A male subject roughly 80 years of age — 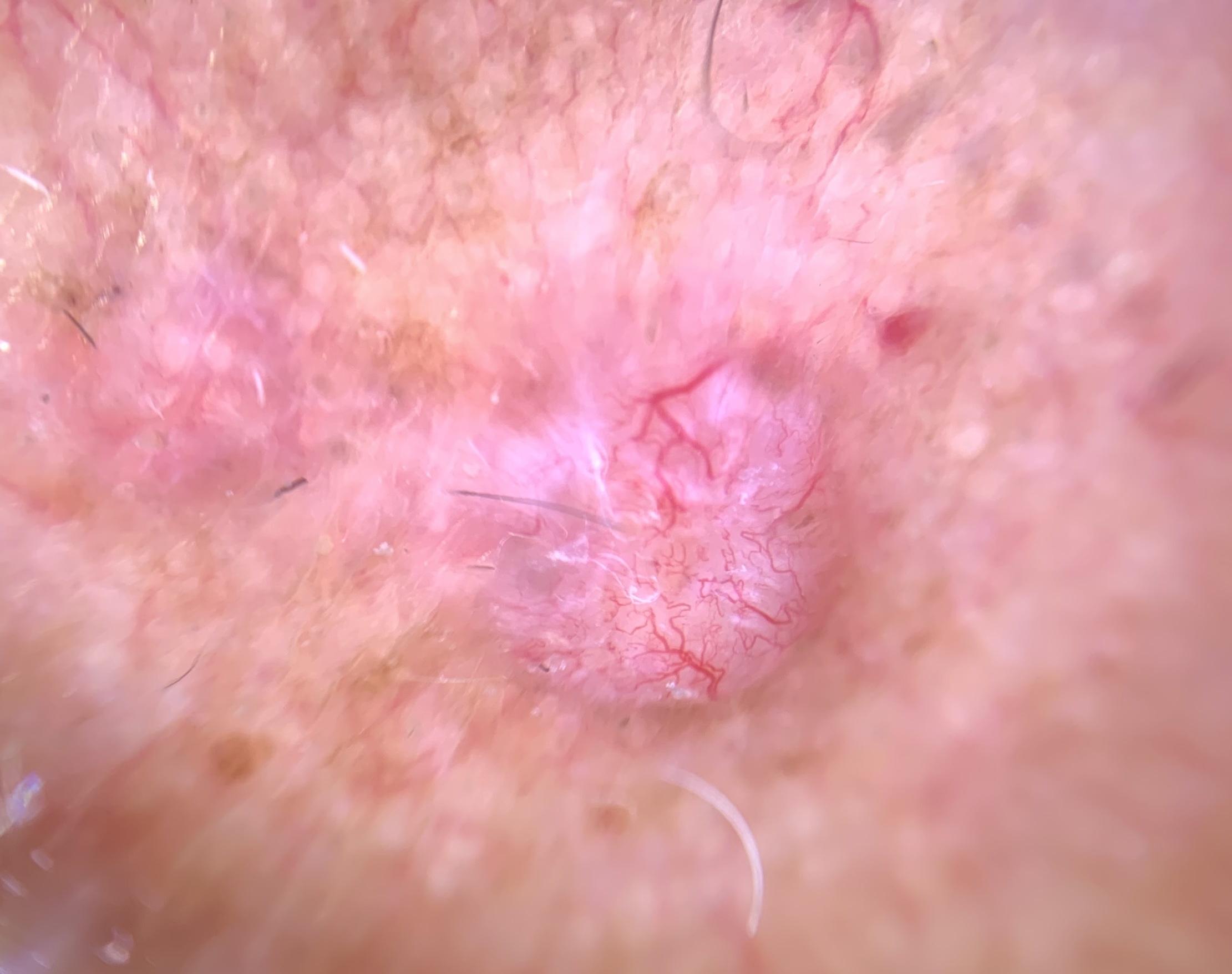The lesion is on the head or neck. Histopathological examination showed a malignant, adnexal lesion — a basal cell carcinoma.